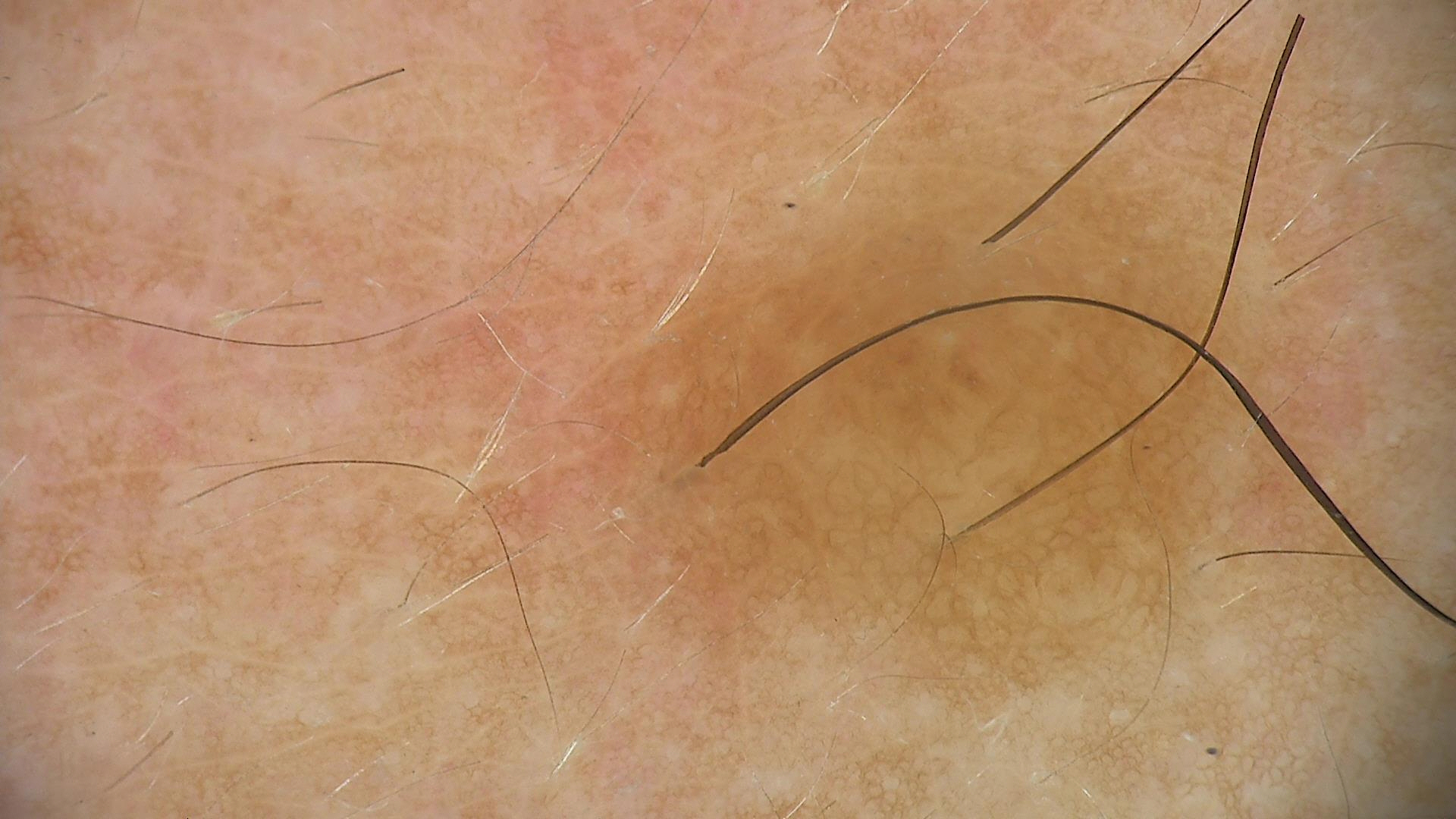class=dermal nevus (expert consensus)